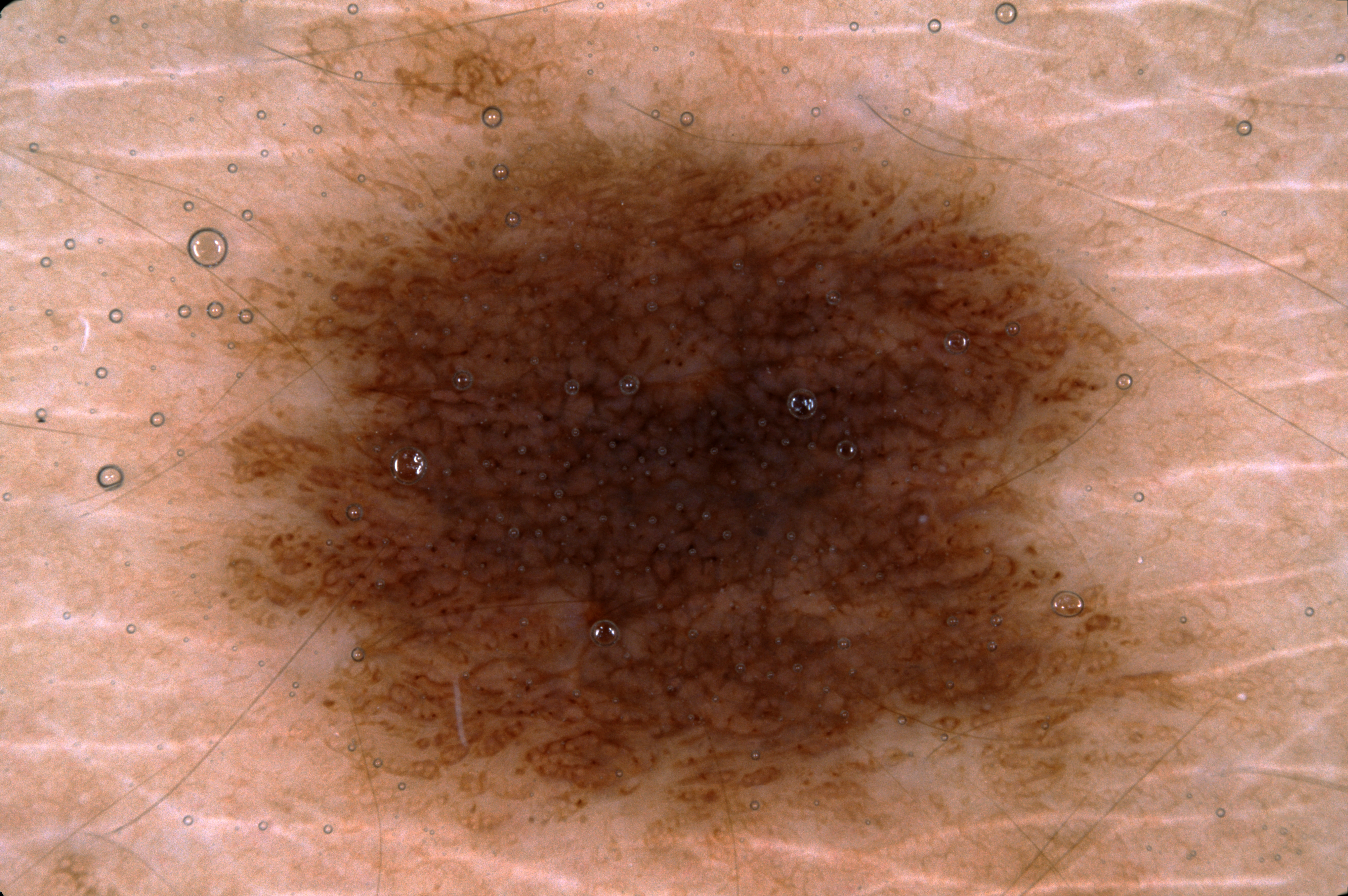imaging — dermoscopic image
patient — female, aged around 30
location — 211, 49, 1179, 847
dermoscopic features — pigment network; absent: milia-like cysts, streaks, and negative network
impression — a melanocytic nevus, a benign skin lesion